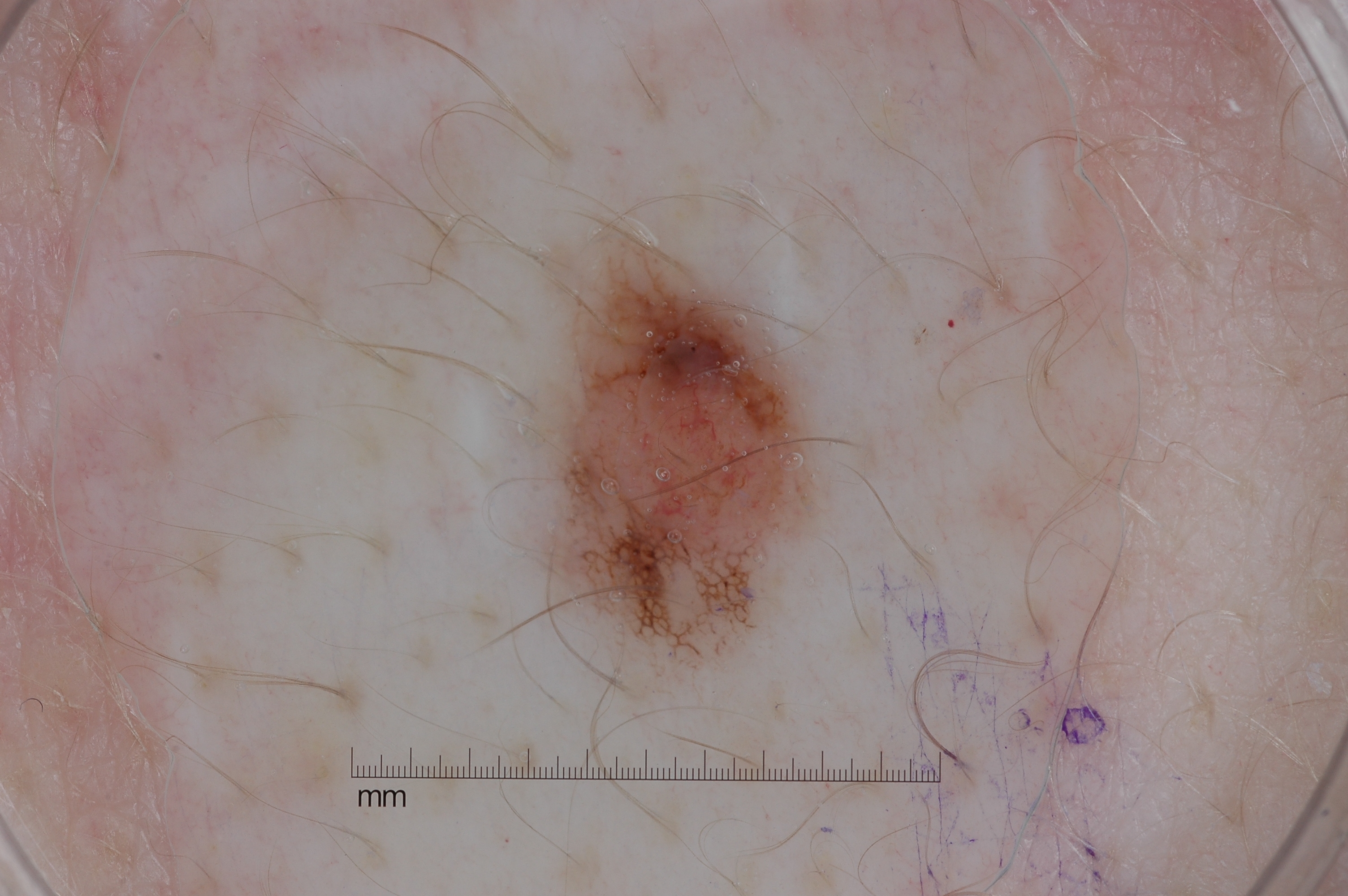modality = dermoscopy | patient = female, aged approximately 45 | dermoscopic findings = pigment network; absent: streaks, milia-like cysts, and negative network | lesion location = x1=548 y1=245 x2=811 y2=658 | diagnosis = a melanocytic nevus, a benign lesion.